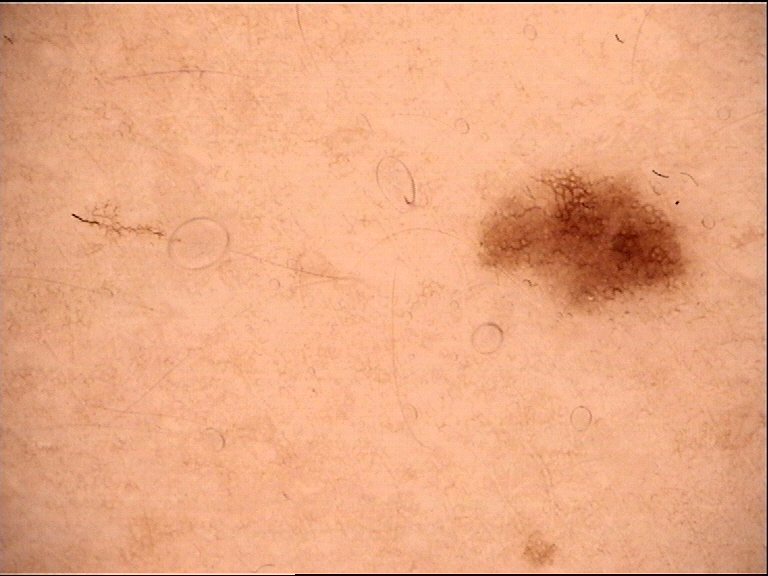Findings:
- label — dysplastic junctional nevus (expert consensus)